The patient is 40–49, male; located on the arm; an image taken at a distance: 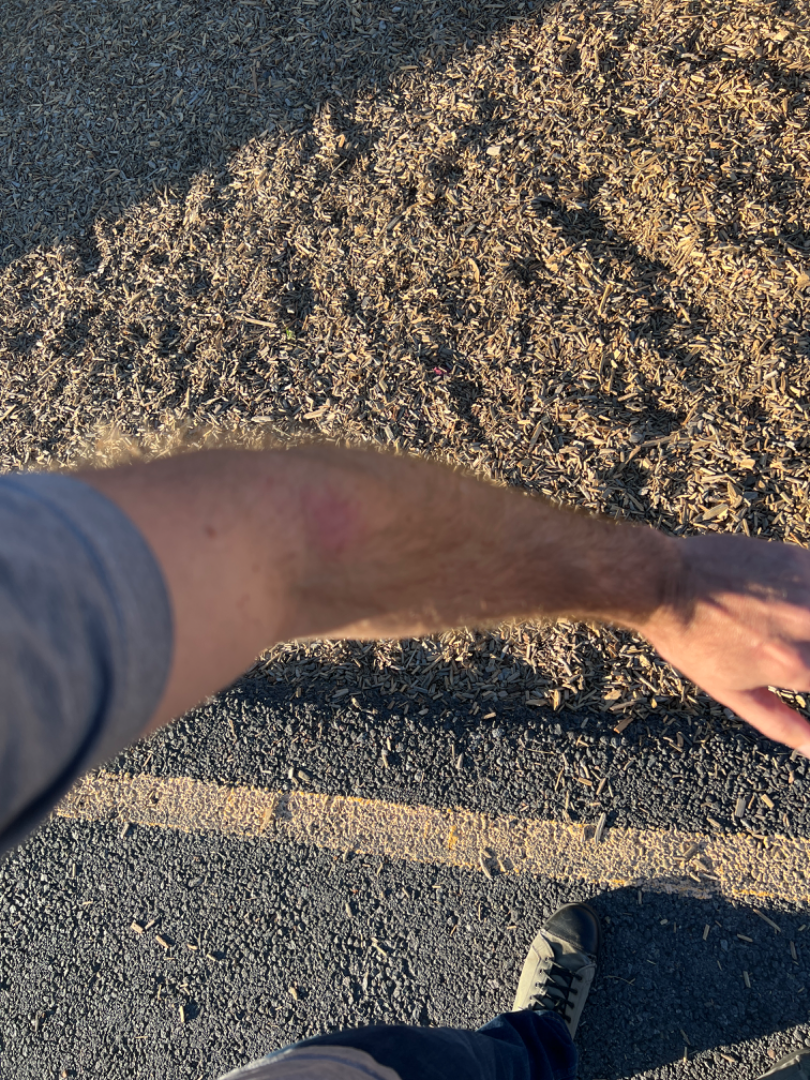Most consistent with Allergic Contact Dermatitis.